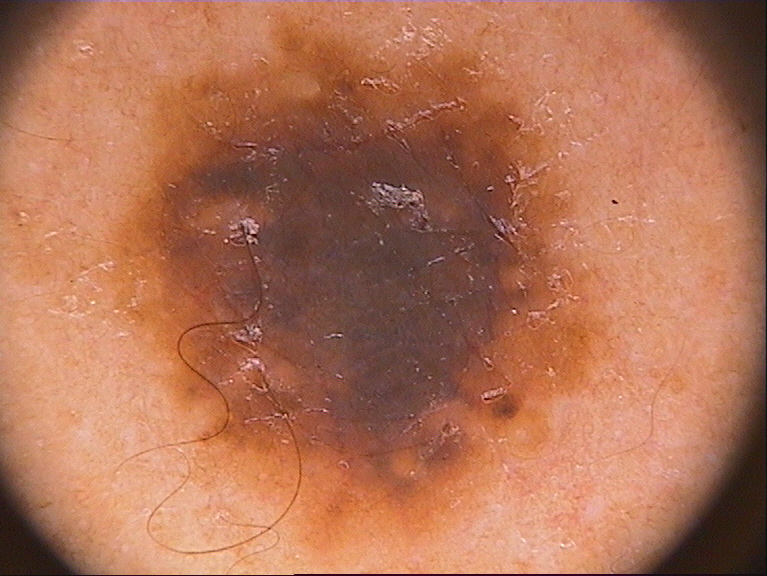A dermoscopic image of a skin lesion.
A male subject, approximately 30 years of age.
Dermoscopy demonstrates no milia-like cysts, negative network, streaks, globules, or pigment network.
A large lesion occupying much of the field.
The visible lesion spans bbox=[80, 11, 633, 563].
The diagnostic assessment was a melanocytic nevus, a benign lesion.